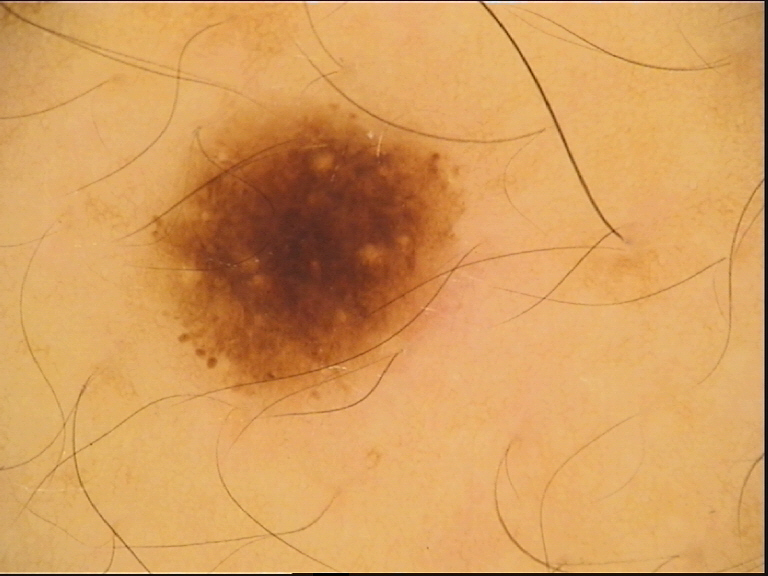Case:
A dermoscopic photograph of a skin lesion.
Conclusion:
The diagnosis was a benign lesion — a dysplastic junctional nevus.